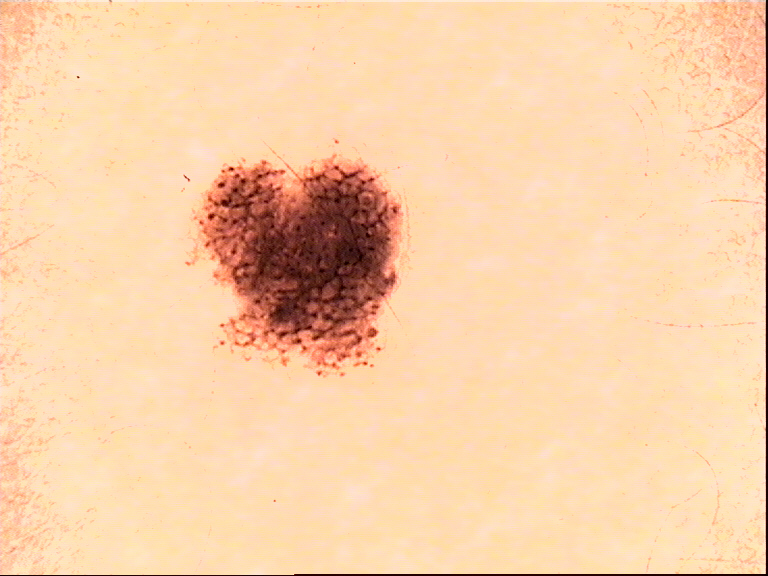Classified as a banal lesion — a compound nevus.